A dermoscopic close-up of a skin lesion: 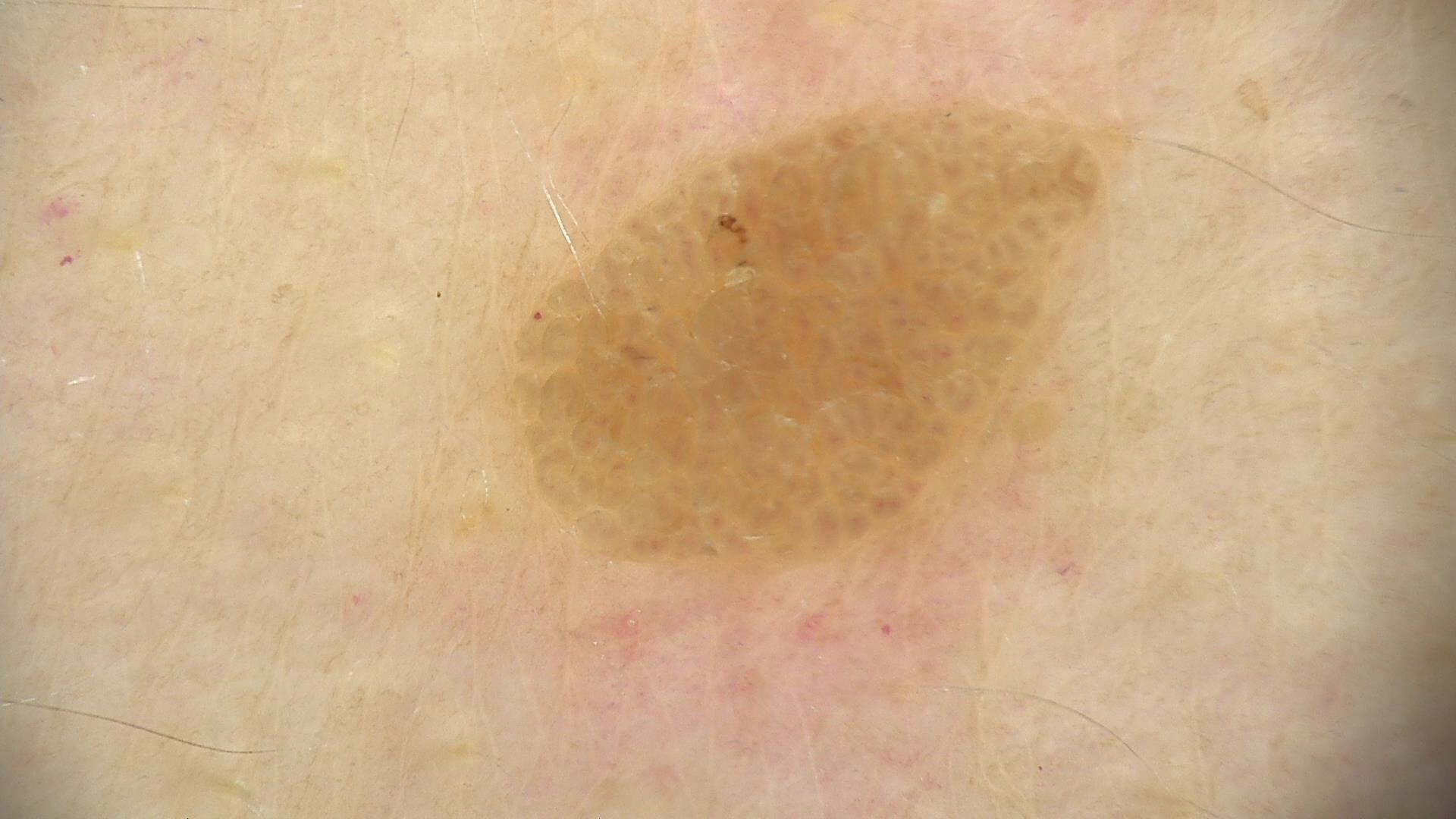Conclusion: The diagnostic label was a benign, keratinocytic lesion — a seborrheic keratosis.